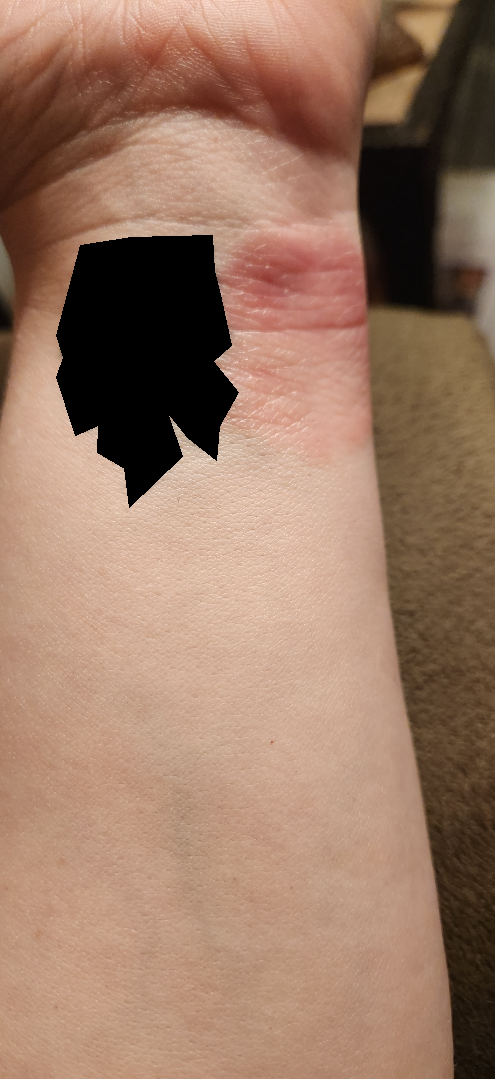image framing: at an angle; patient: female, age 30–39; assessment: the differential is split between Chronic dermatitis, NOS and Allergic Contact Dermatitis.